A dermoscopic image of a skin lesion:
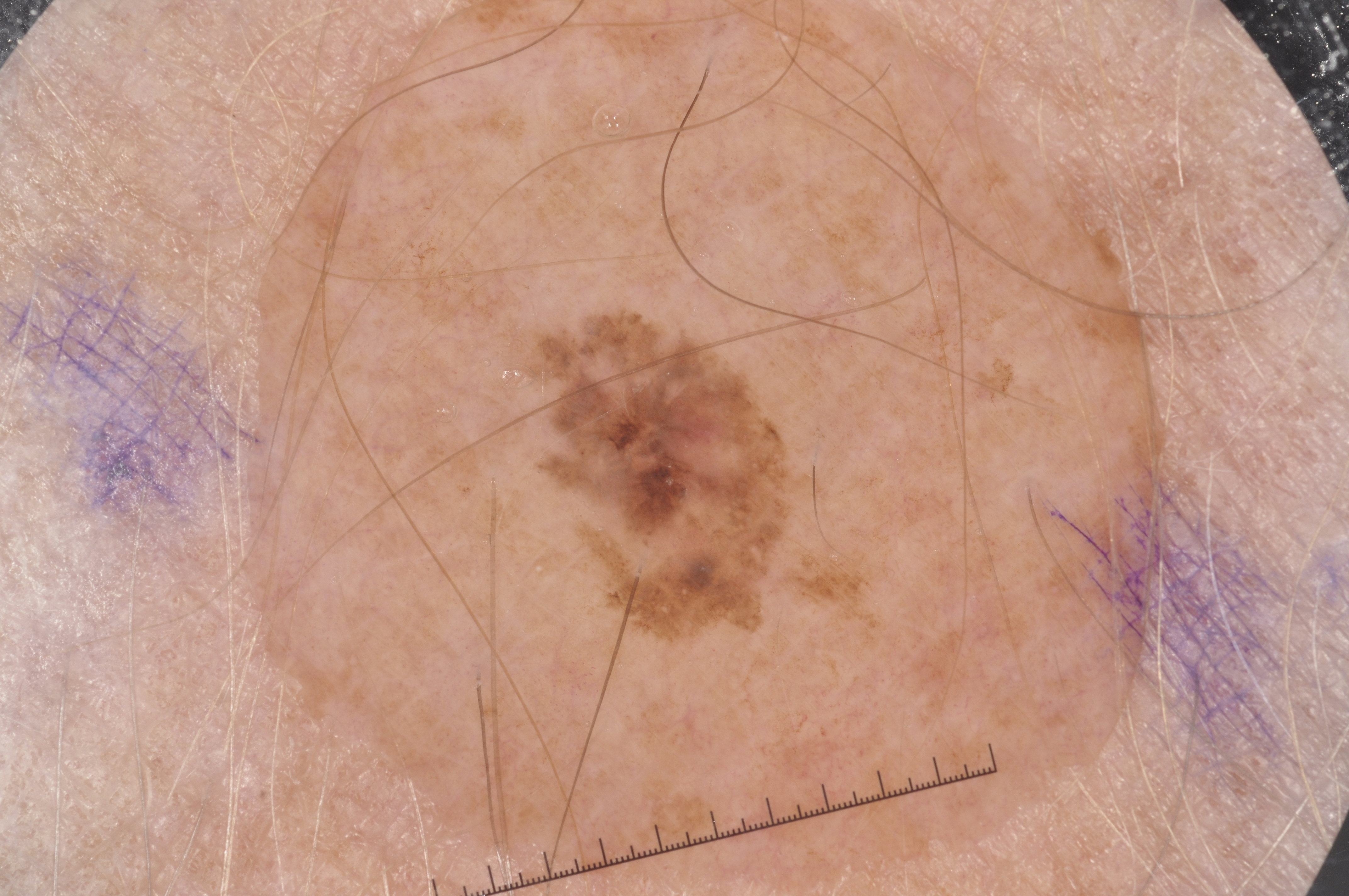| field | value |
|---|---|
| size | ~7% of the field |
| location | [510,307,824,658] |
| absent dermoscopic findings | streaks, negative network, milia-like cysts, and pigment network |
| diagnostic label | a melanoma |